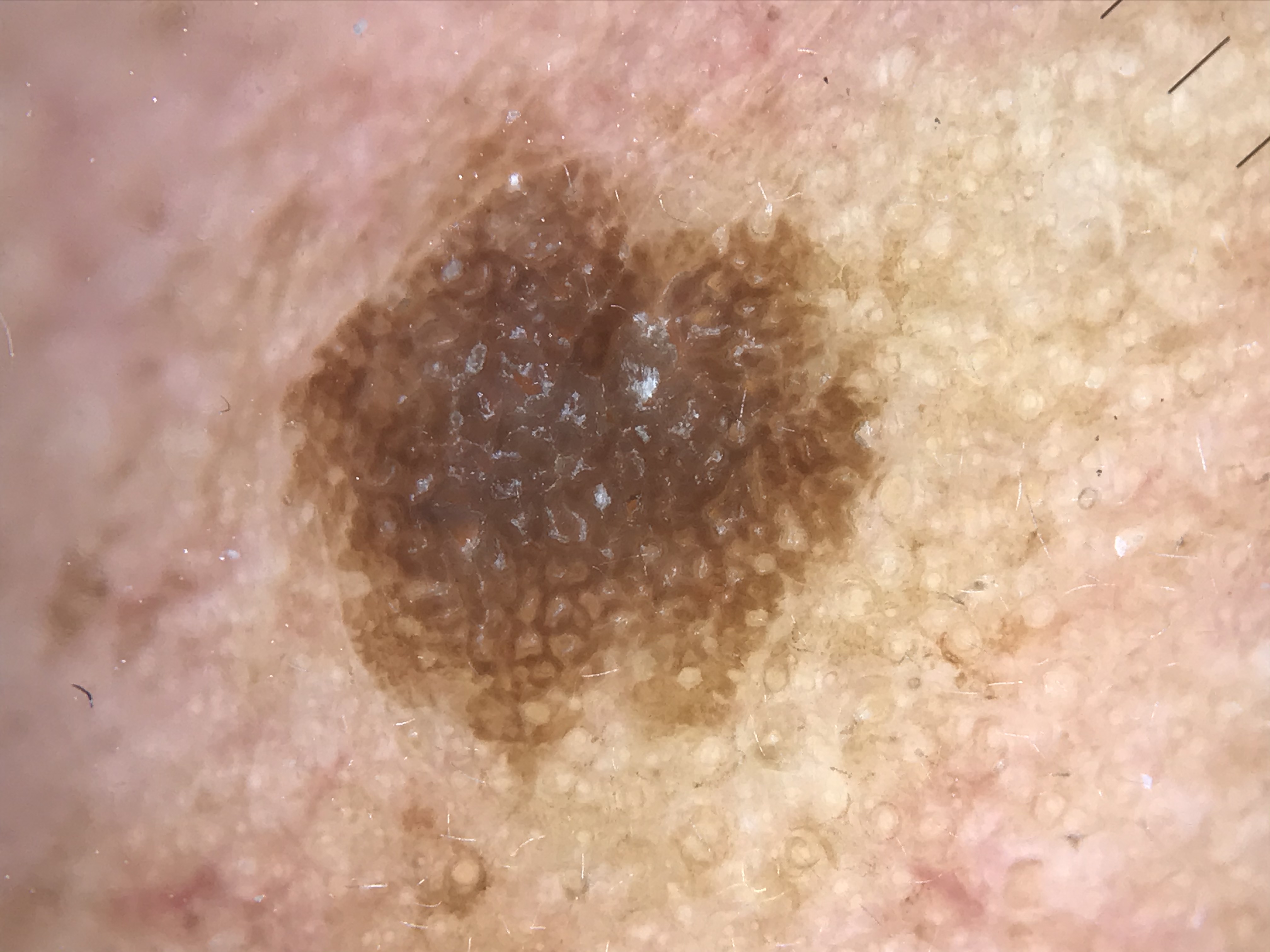A dermatoscopic image of a skin lesion.
The morphology is that of a keratinocytic lesion.
Diagnosed as a seborrheic keratosis.